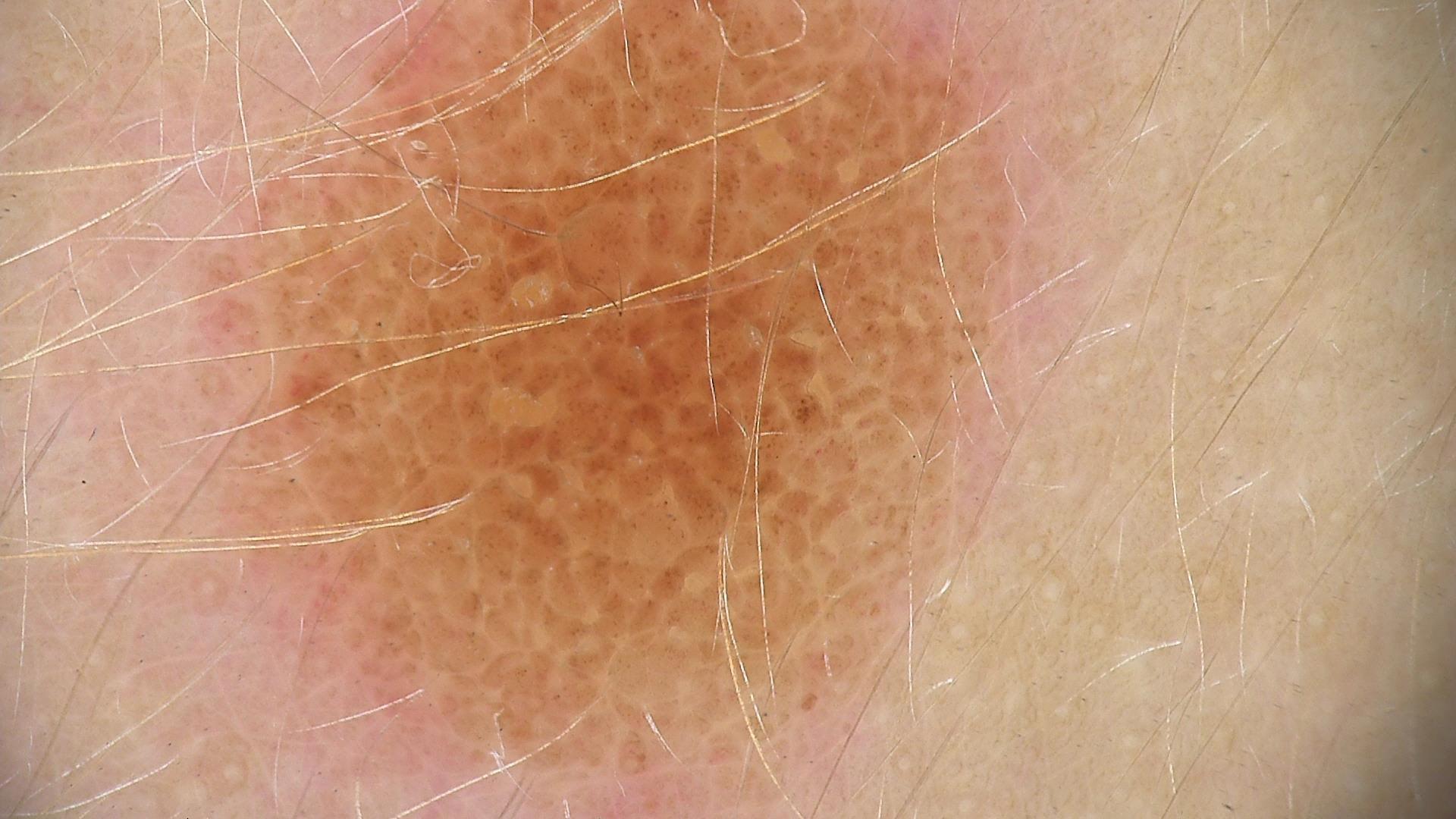Labeled as a dysplastic compound nevus.